Female subject, age 40–49; an image taken at an angle; located on the arm, head or neck, back of the torso and front of the torso.
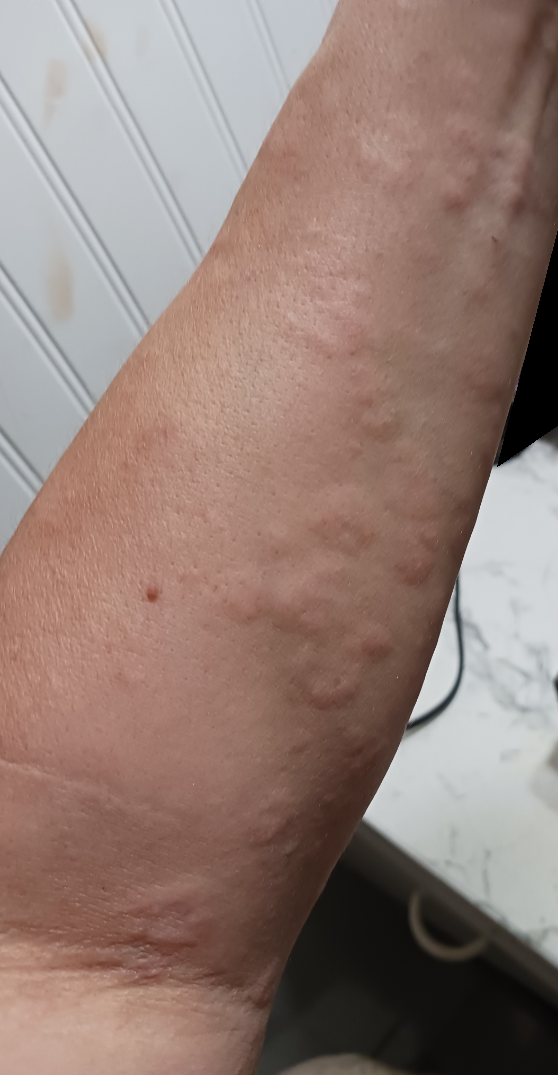| feature | finding |
|---|---|
| assessment | indeterminate |